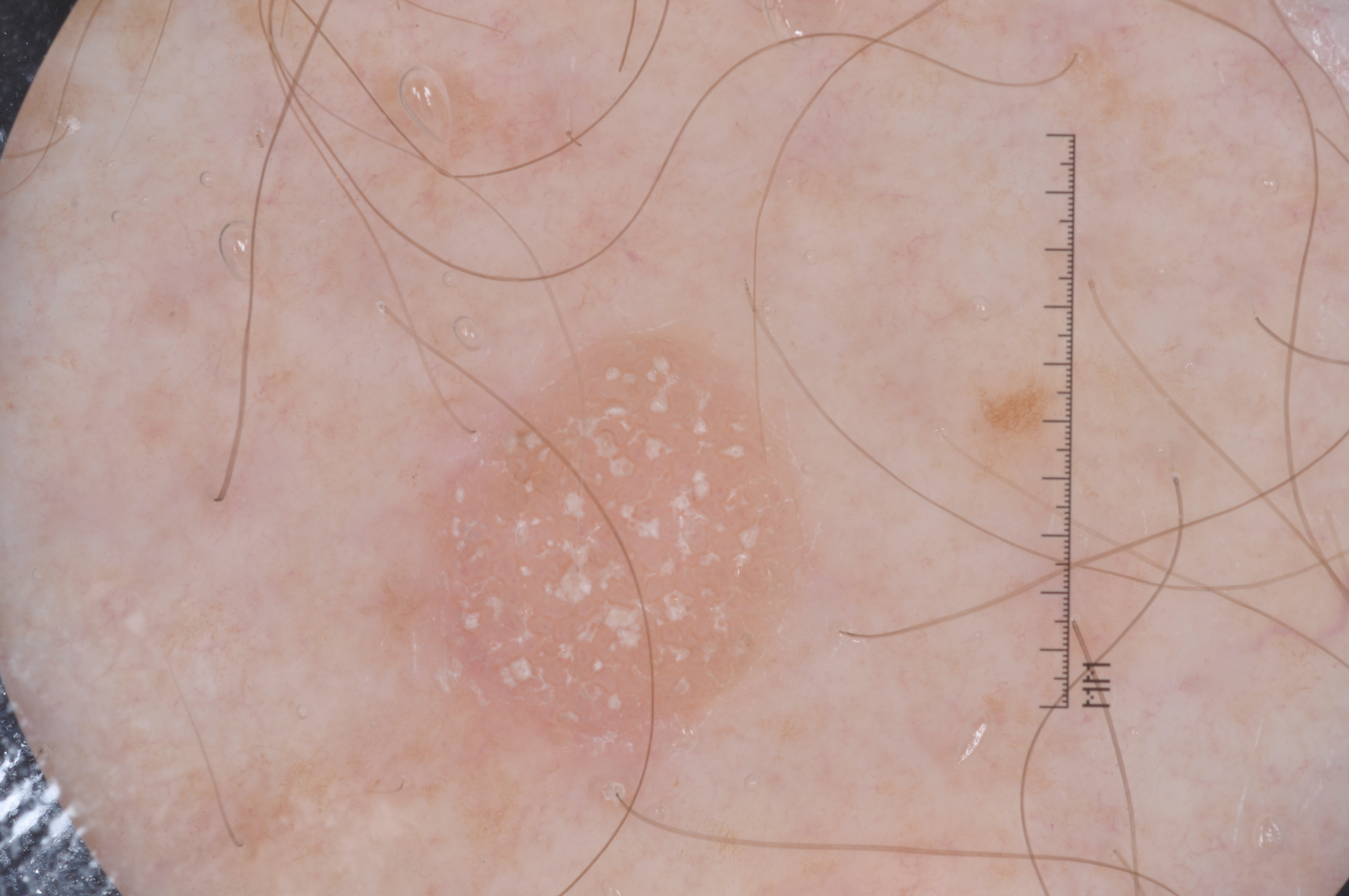Case summary:
- patient — male, about 70 years old
- imaging — dermatoscopic image of a skin lesion
- lesion bbox — <box>369, 337, 811, 784</box>
- absent dermoscopic findings — streaks, milia-like cysts, pigment network, and negative network
- diagnosis — a seborrheic keratosis